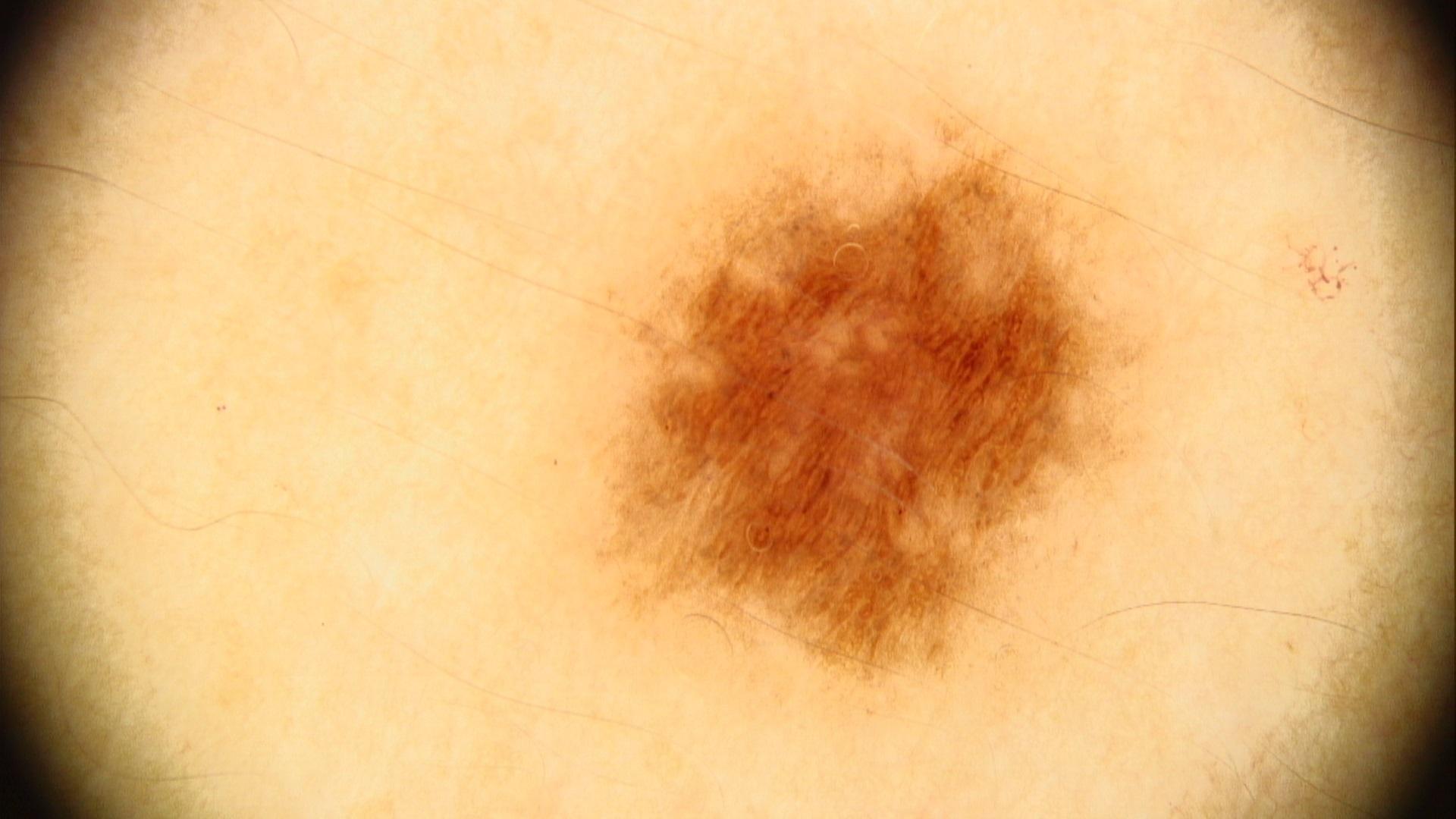Q: Patient demographics?
A: female, approximately 30 years of age
Q: What is the patient's skin type?
A: III
Q: What is the anatomic site?
A: the trunk
Q: What was the clinical impression?
A: Nevus